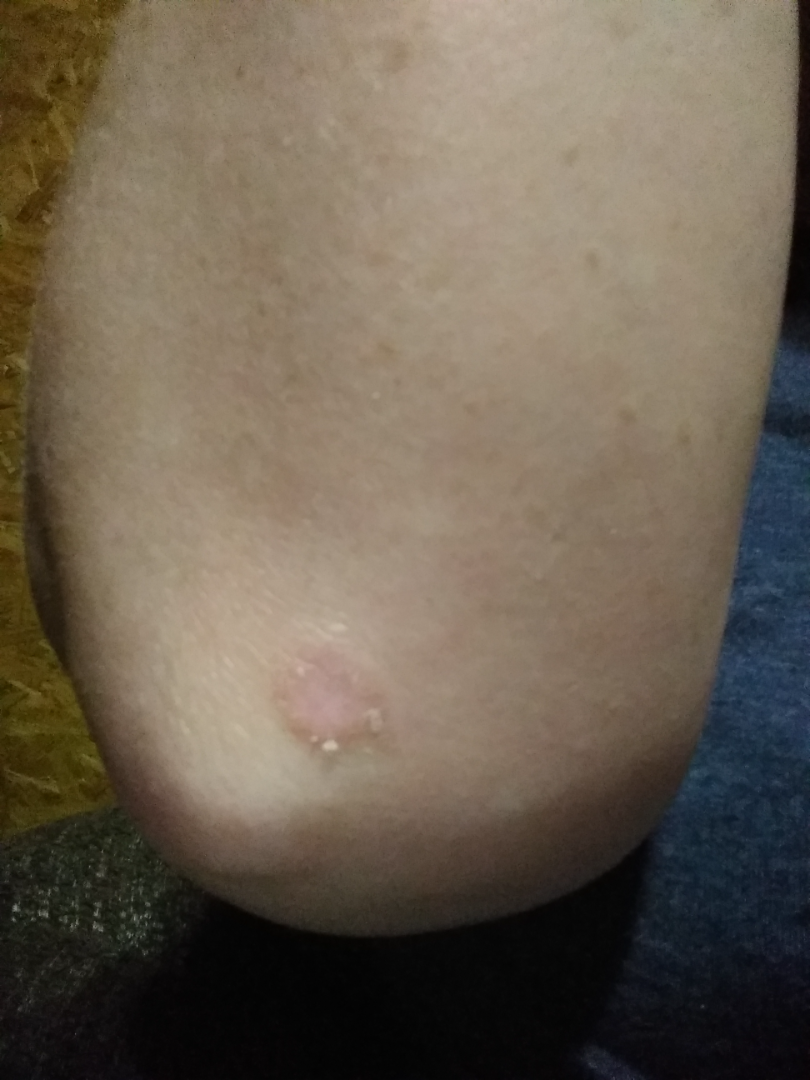History: Skin tone: FST III; human graders estimated 3 on the MST. Texture is reported as raised or bumpy and rough or flaky. Located on the arm. Female patient, age 30–39. This is a close-up image. The patient reported no systemic symptoms. The lesion is associated with enlargement. Impression: Tinea, Psoriasis and Eczema were considered with similar weight.